Contact-polarized dermoscopy of a skin lesion · a male subject aged 18 to 22.
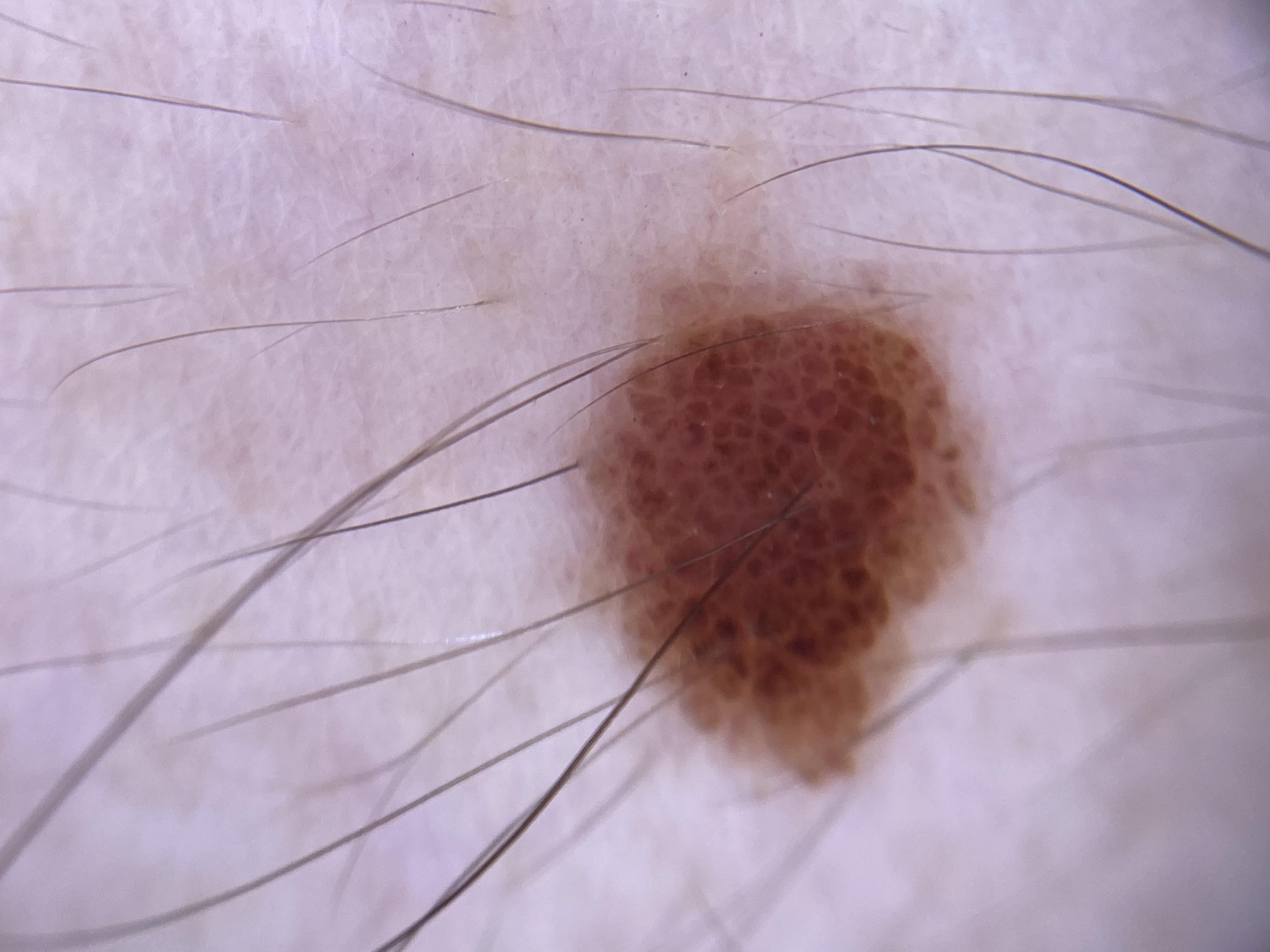Q: What is the anatomic site?
A: the trunk
Q: What is this lesion?
A: Nevus (clinical impression)